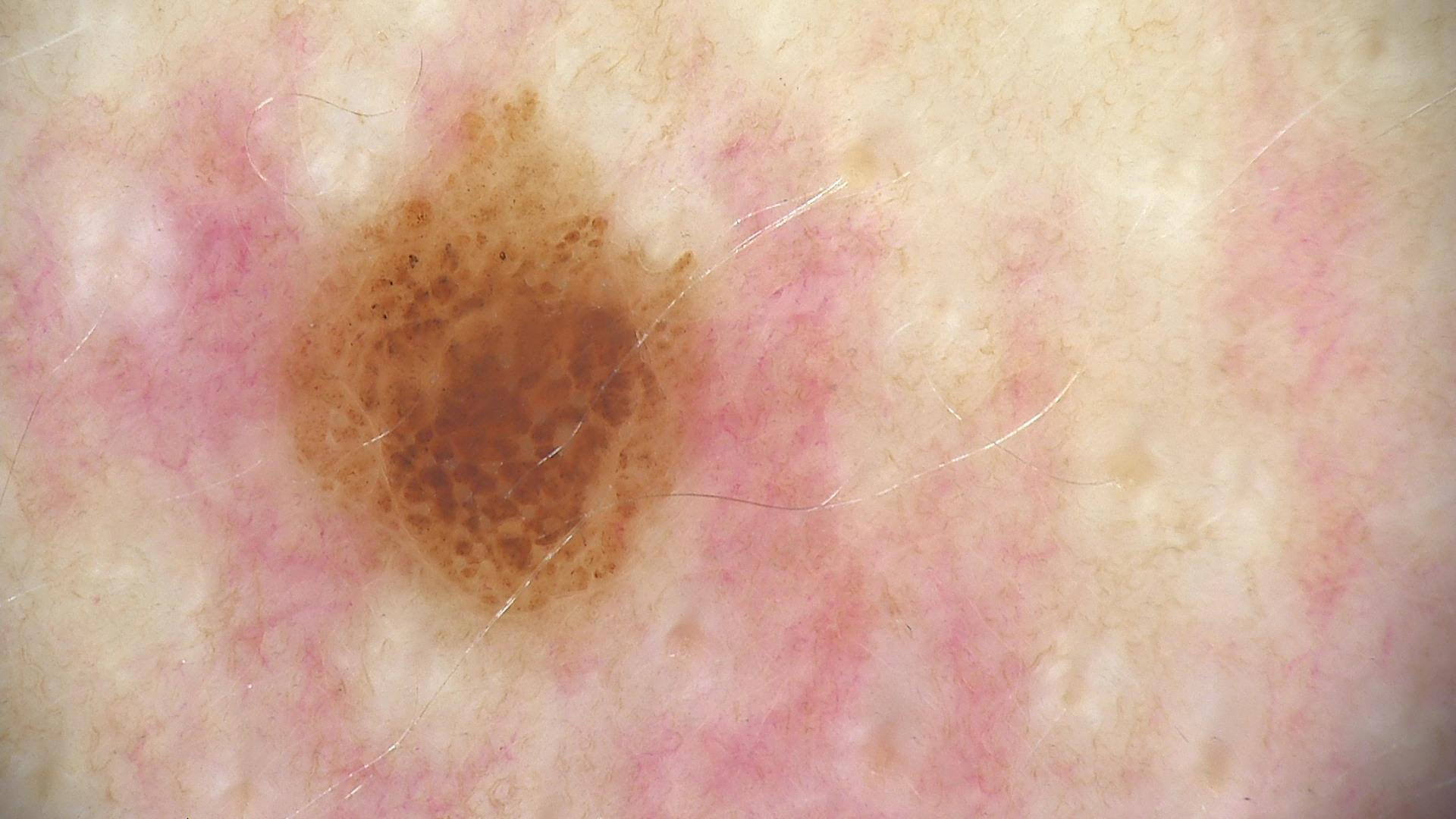Diagnosed as a compound nevus.